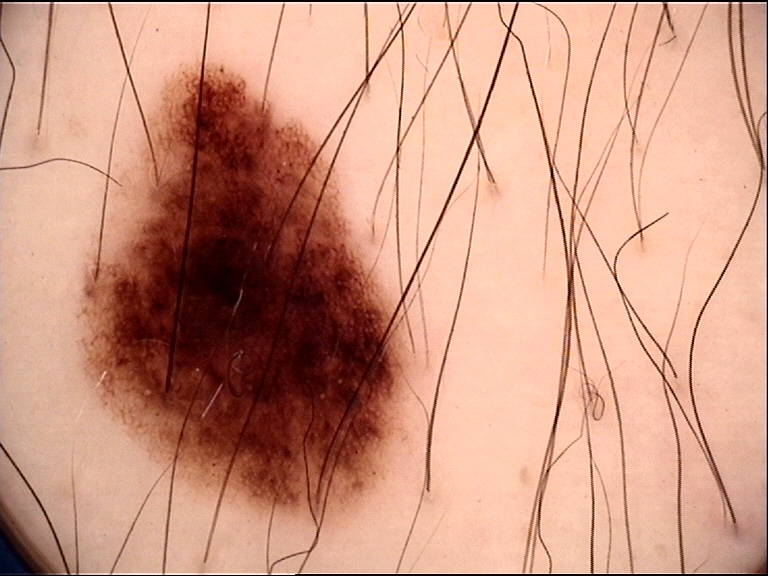image=dermatoscopy; diagnosis=dysplastic junctional nevus (expert consensus).